The patient reports a personal history of cancer · a clinical photograph of a skin lesion · the patient says their skin tans without first burning · the patient describes having a moderate number of moles · a male subject 65 years of age · collected as part of a research study, without a referral diagnosis:
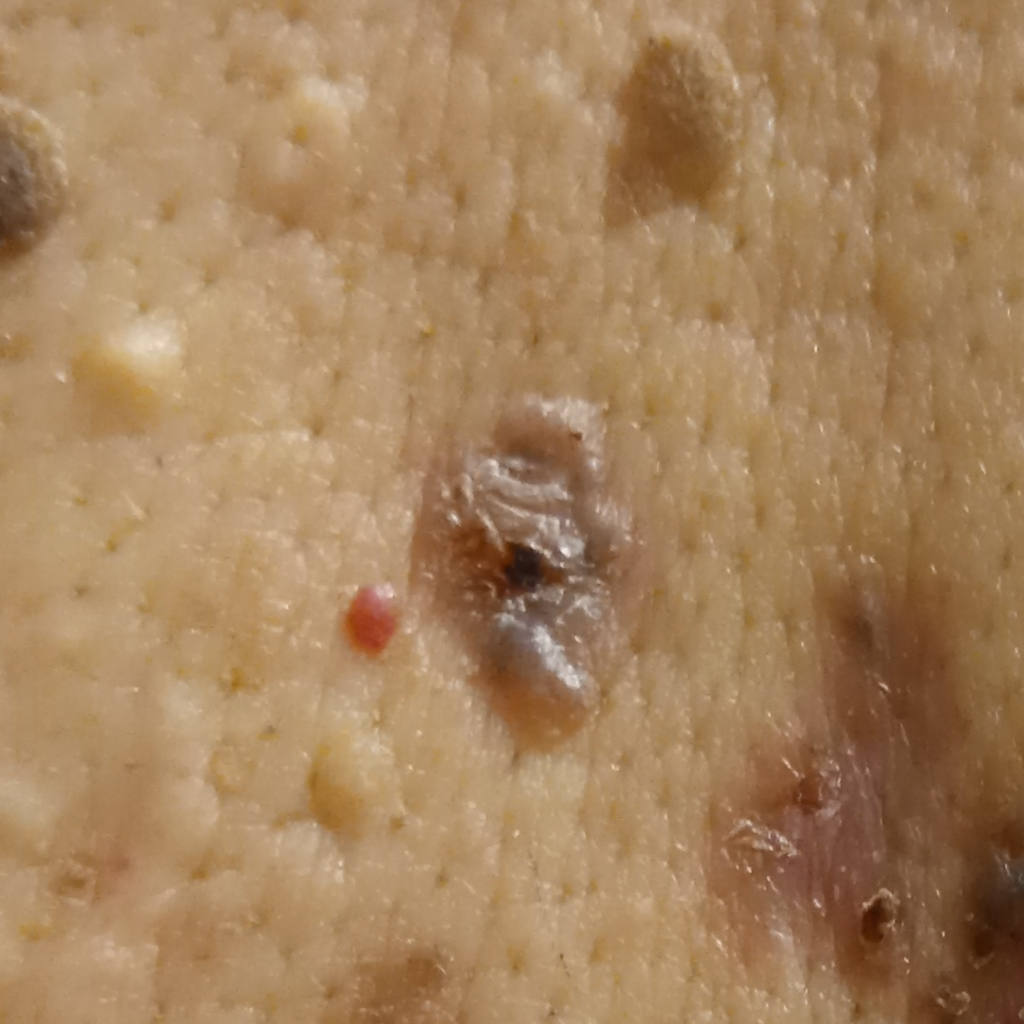anatomic site=the back | diameter=11.9 mm | diagnosis=basal cell carcinoma (dermatologist consensus).